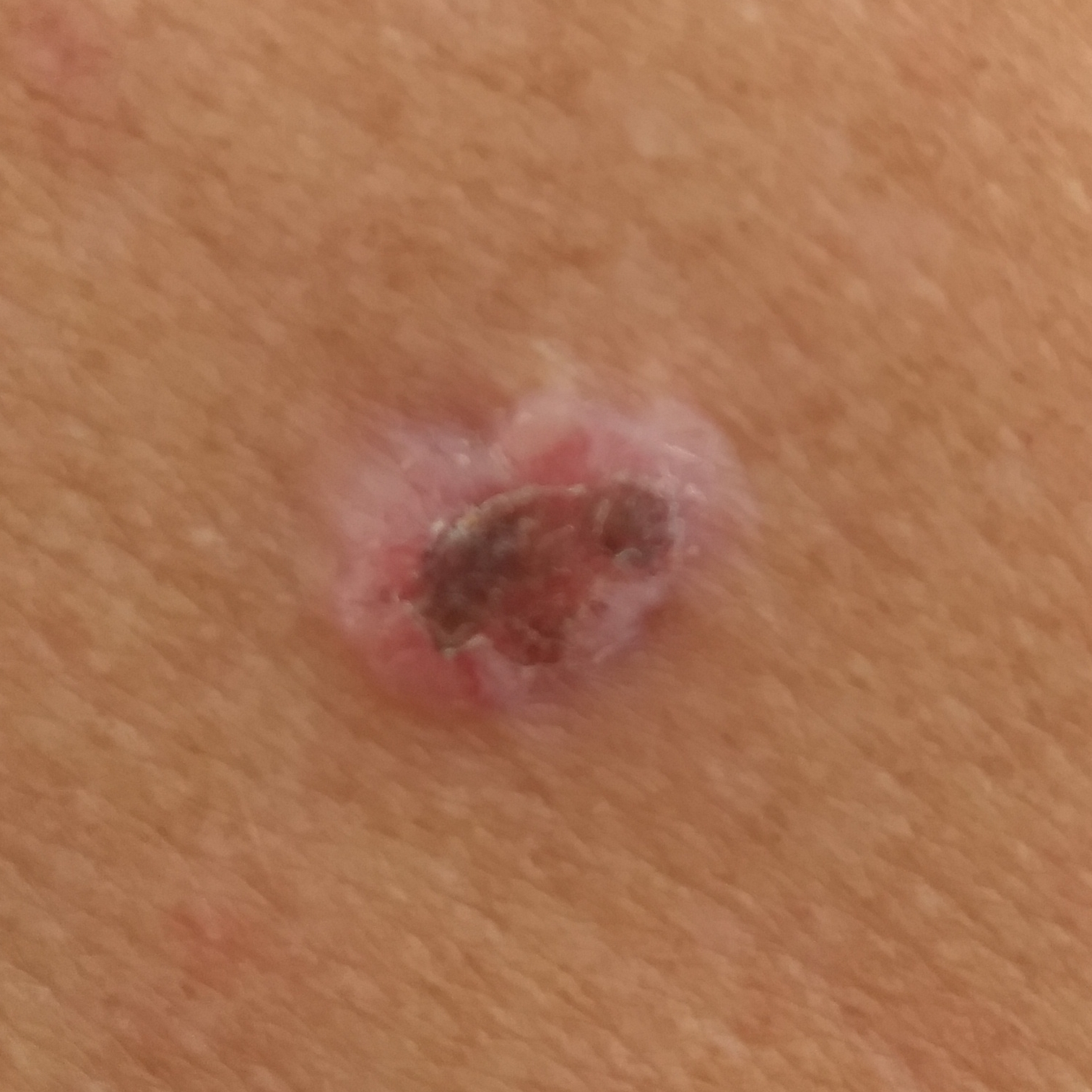Clinical context: A male patient 62 years of age. Recorded as Fitzpatrick II. By history, alcohol use and pesticide exposure. A clinical photograph of a skin lesion. The lesion is located on the back. The lesion measures 15 × 11 mm. The patient describes that the lesion has changed, has grown, and is elevated. Diagnosis: Histopathologically confirmed as a skin cancer — a basal cell carcinoma.